The photograph is a close-up of the affected area · the patient is 40–49, female.
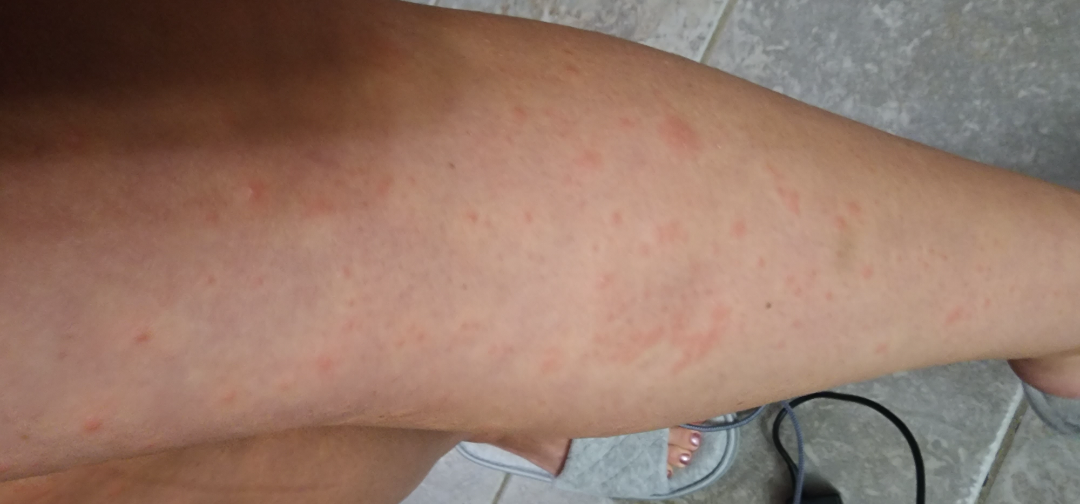dermatologist impression: Acute vesicular dermatitis (0.41); Allergic Contact Dermatitis (0.41); Insect Bite (0.18).